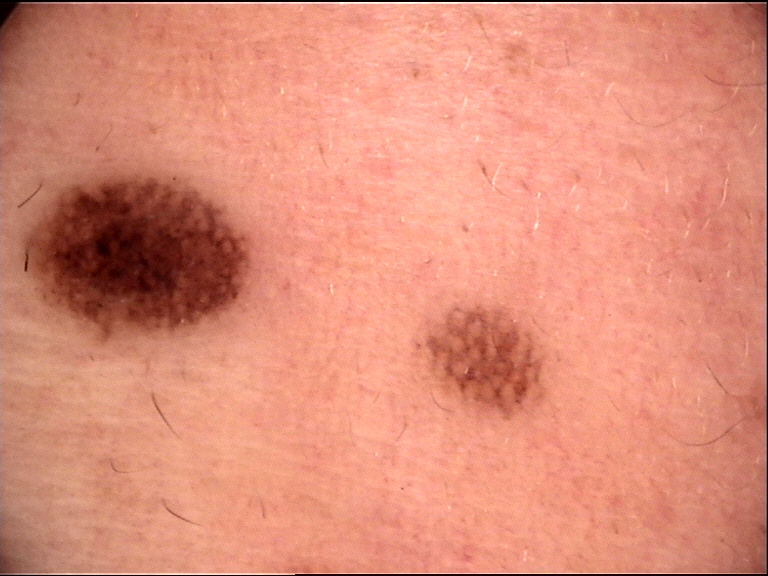Findings:
– image type · dermatoscopy
– class · Miescher nevus (expert consensus)